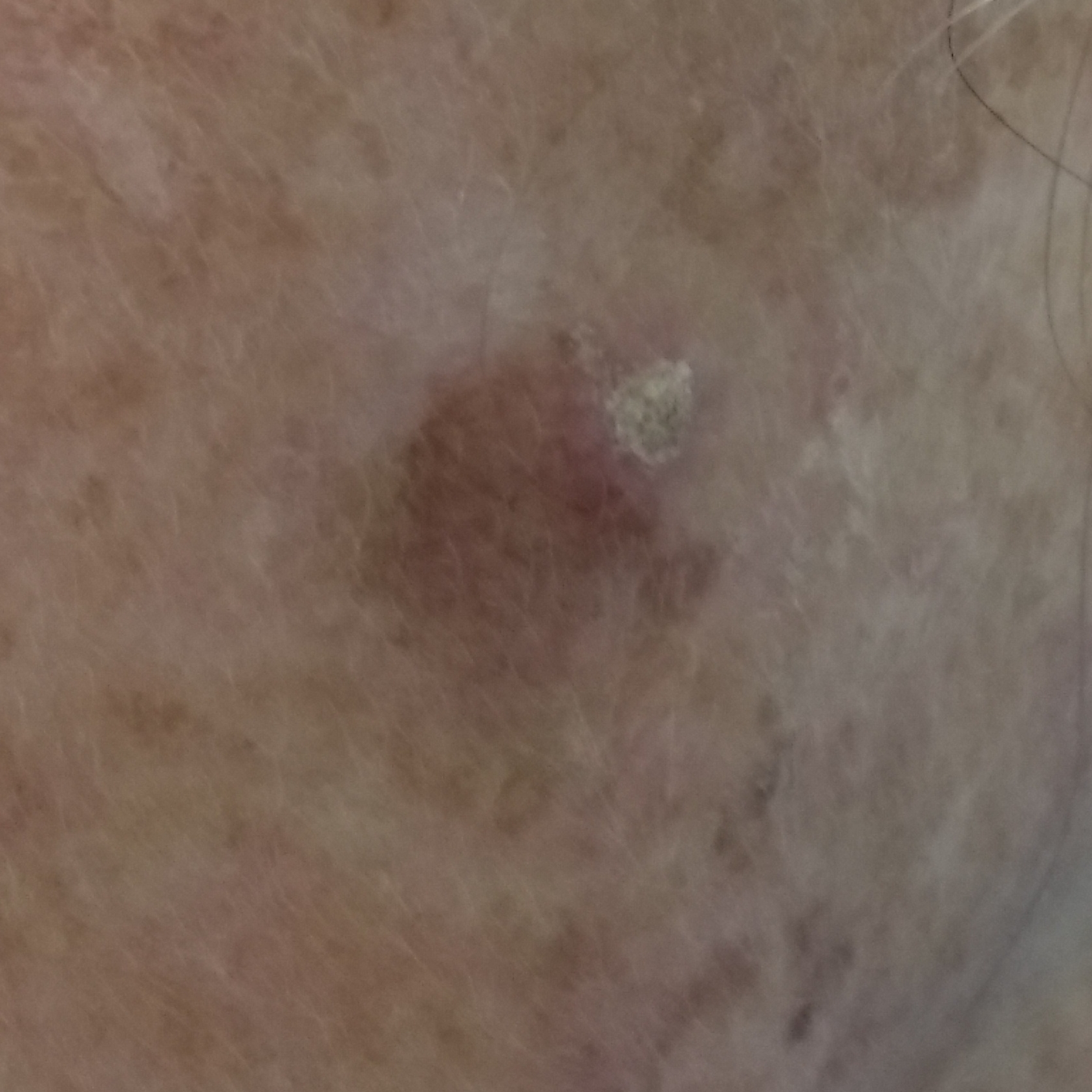risk factors: prior malignancy (patient or family) | patient: female, in their early 60s | modality: smartphone clinical photo | FST: III | anatomic site: the face | lesion size: 5 × 5 mm | reported symptoms: growth, change in appearance, elevation / no itching | diagnosis: actinic keratosis (biopsy-proven).